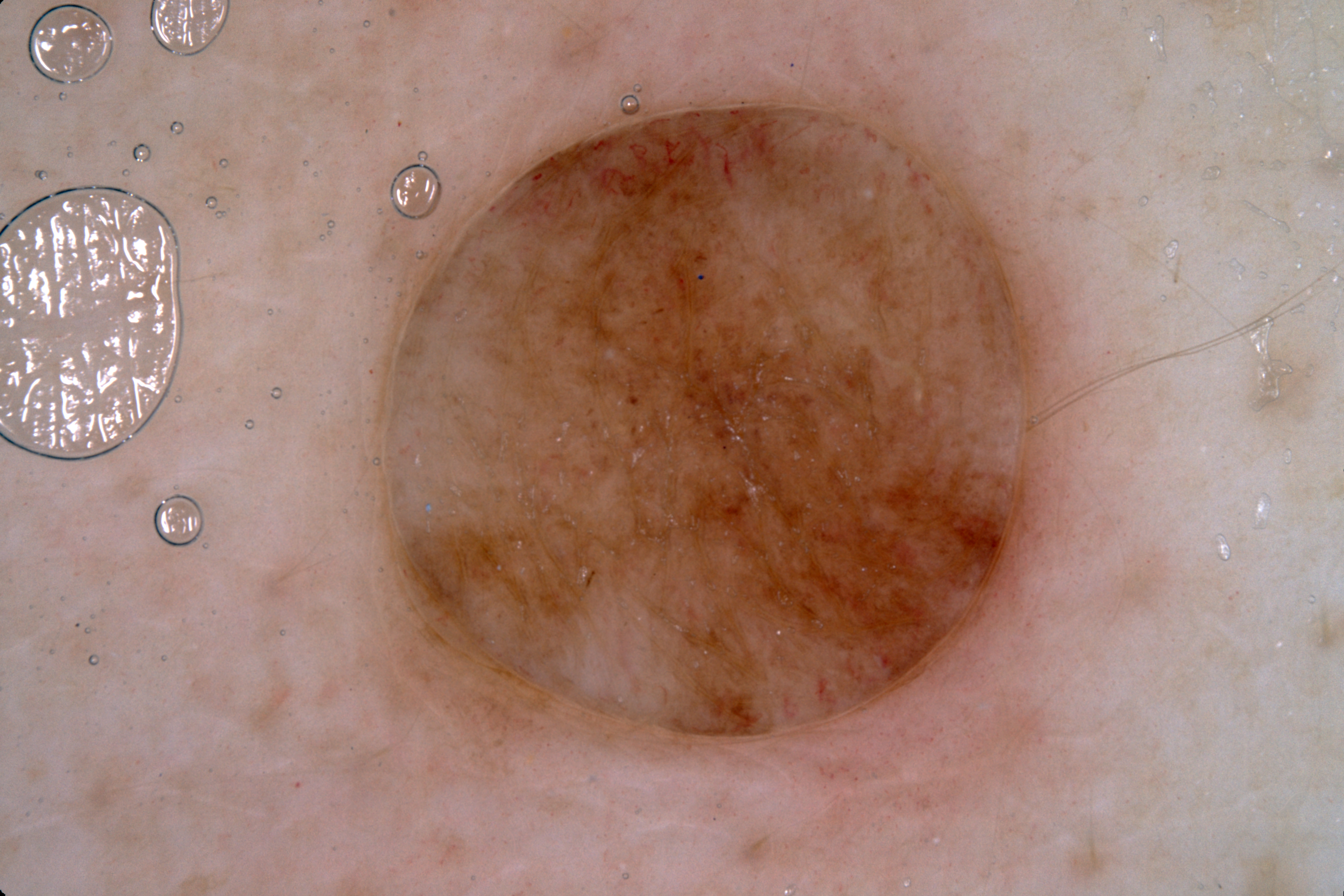Findings: A dermoscopic image of a skin lesion. Dermoscopic assessment notes milia-like cysts, with no pigment network, streaks, or negative network. A large lesion occupying much of the field. Lesion location: x1=367 y1=84 x2=1092 y2=763. Conclusion: The clinical diagnosis was a melanocytic nevus, a benign skin lesion.